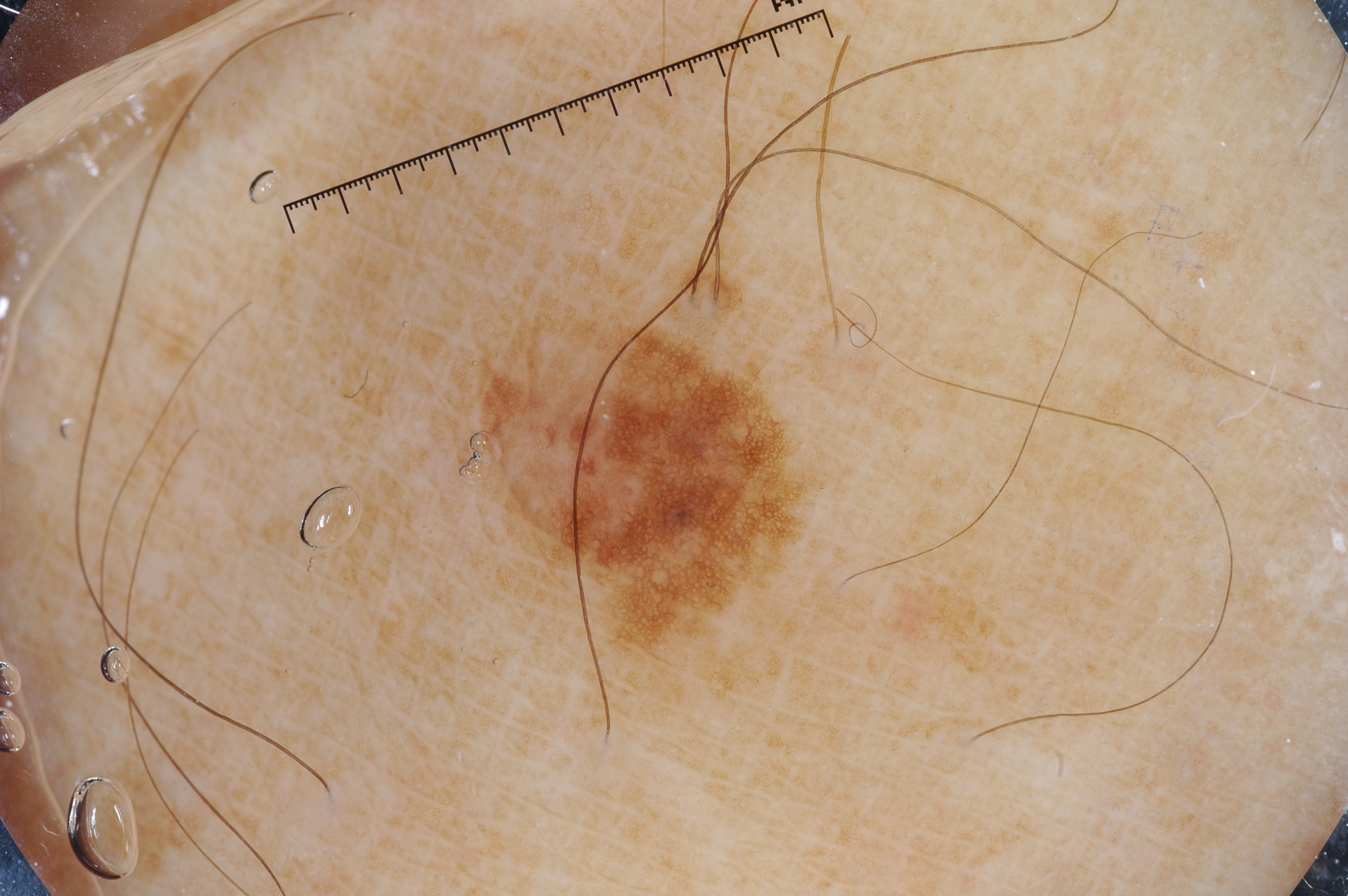A male patient aged 63-67. A dermatoscopic image of a skin lesion. The lesion's extent is left=474, top=322, right=801, bottom=644. Dermoscopy demonstrates pigment network and milia-like cysts. Expert review diagnosed this as a melanocytic nevus, a benign skin lesion.